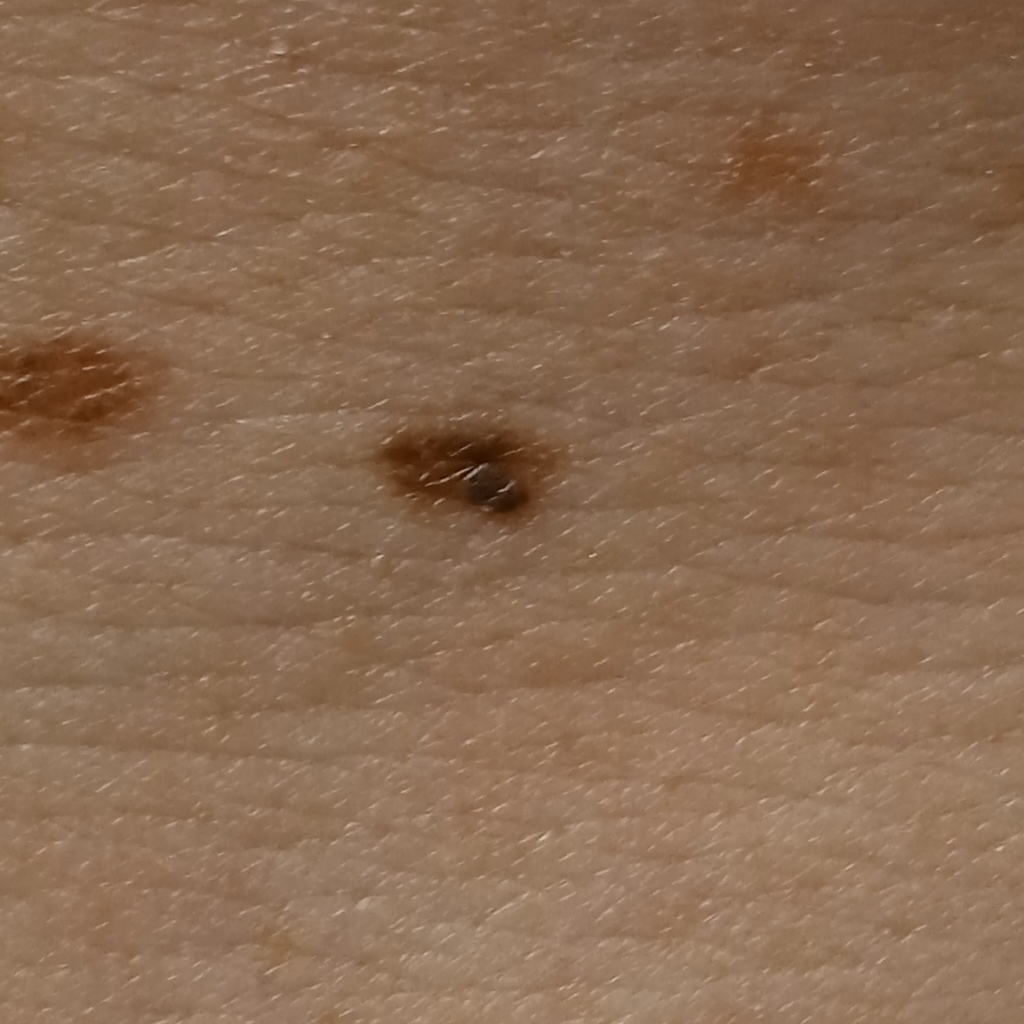Q: Tell me about the patient.
A: male, 58 years of age
Q: What is the patient's nevus burden?
A: numerous melanocytic nevi
Q: What kind of image is this?
A: clinical photo
Q: Why was this imaged?
A: clinical suspicion of melanoma
Q: What is the anatomic site?
A: the back
Q: Lesion size?
A: 5.2 mm
Q: What did the biopsy show?
A: melanocytic nevus (biopsy-proven)